The patient says their skin reddens with sun exposure · referred for assessment of suspected basal cell carcinoma · a macroscopic clinical photograph of a skin lesion — 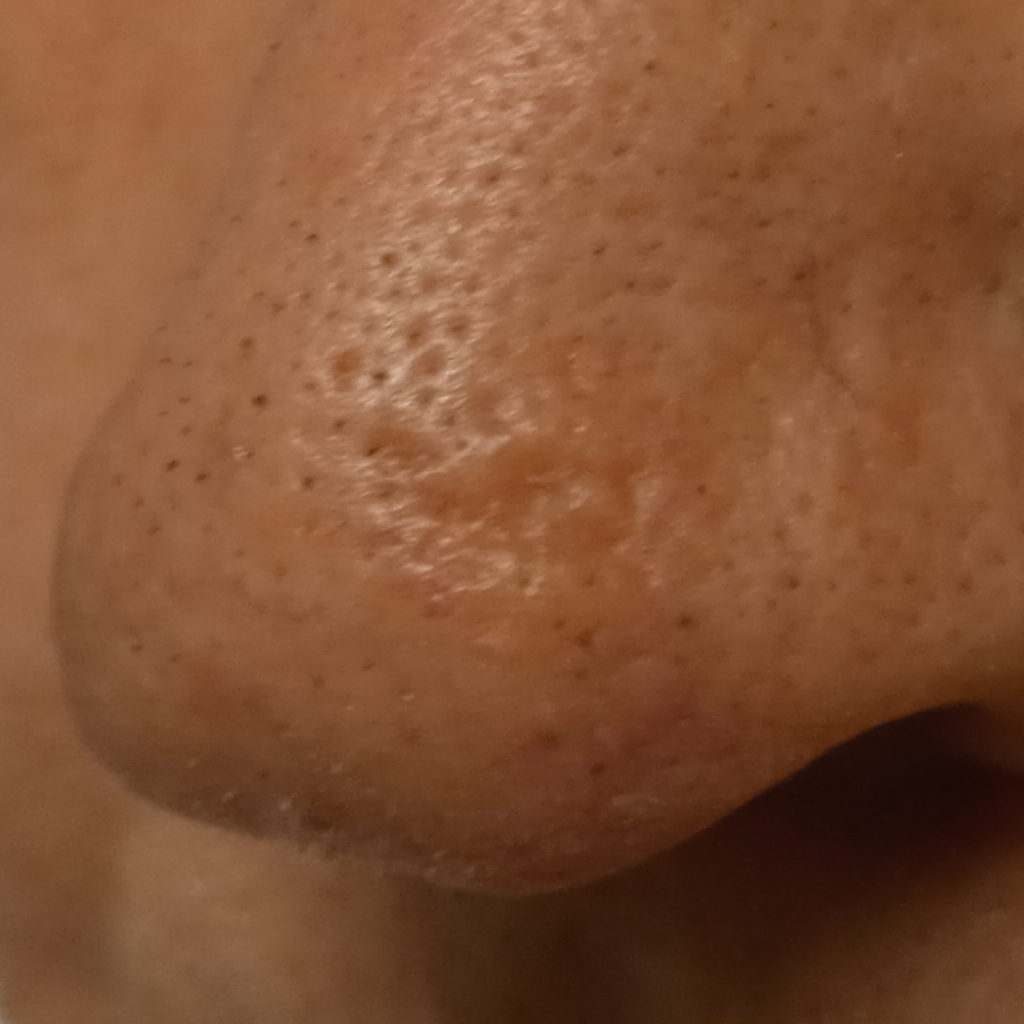The lesion is located on the face.
The biopsy diagnosis was a basal cell carcinoma, following excision, with a measured tumor thickness of 1.7 mm.